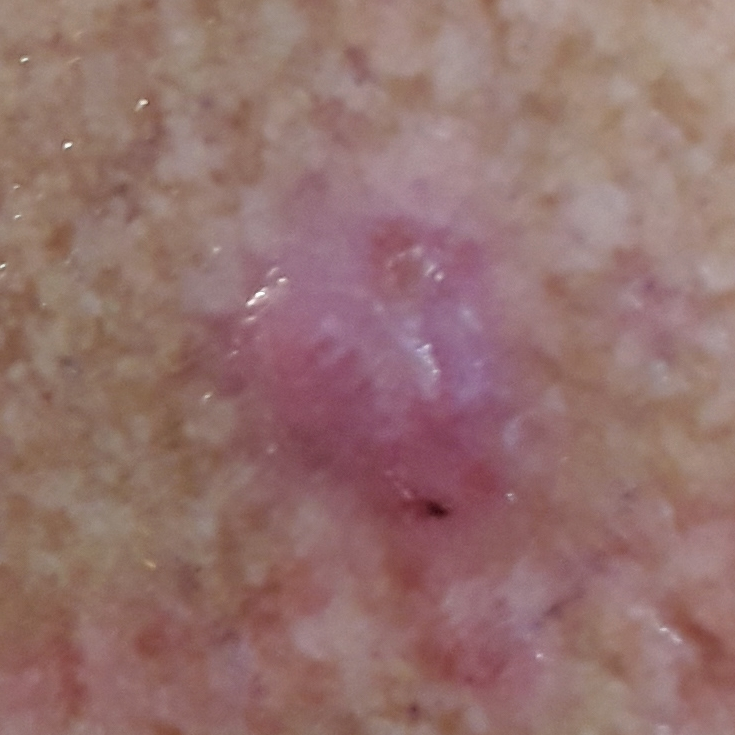Histopathologically confirmed as a basal cell carcinoma.